Located on the front of the torso, back of the hand and arm; present for one to four weeks; the patient considered this a growth or mole; associated systemic symptoms include fatigue; symptoms reported: bleeding, bothersome appearance, itching, burning and pain; texture is reported as raised or bumpy; a close-up photograph; female patient, age 50–59.
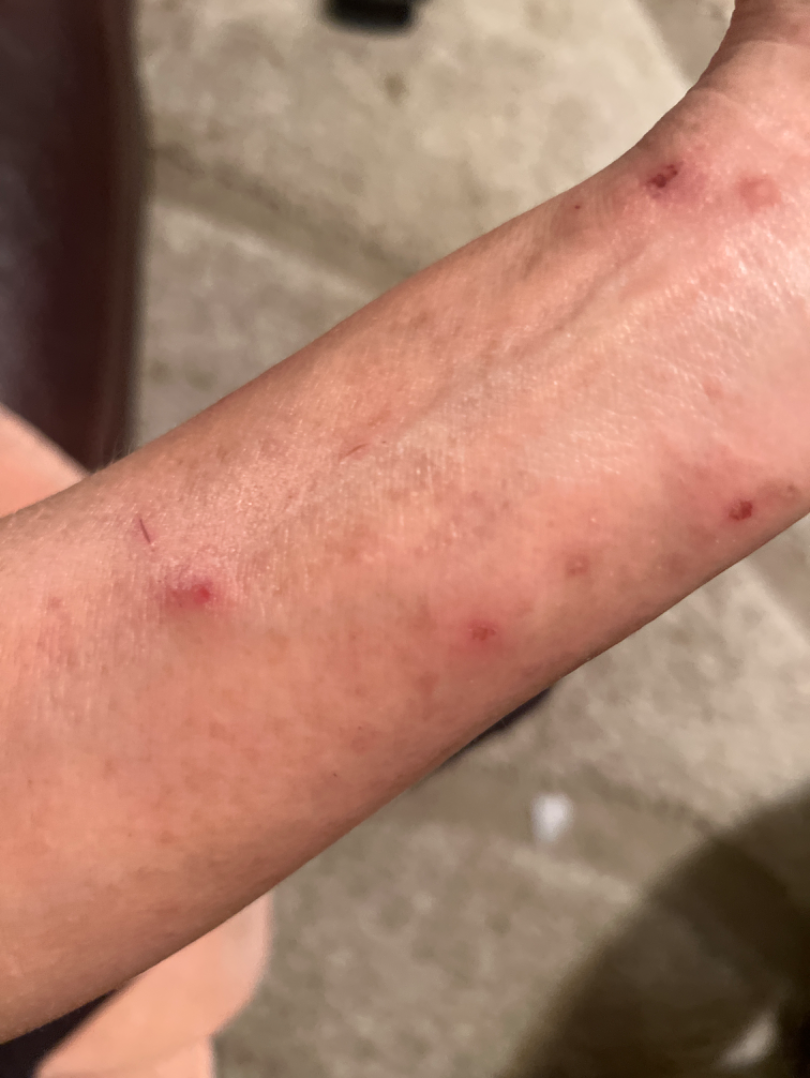On remote dermatologist review, Prurigo nodularis and Abrasion, scrape, or scab were each considered, in no particular order.